The lesion involves the back of the torso and front of the torso · the photo was captured at an angle · the lesion is described as raised or bumpy and rough or flaky · reported lesion symptoms include itching, darkening and enlargement · the patient notes the condition has been present for more than one year:
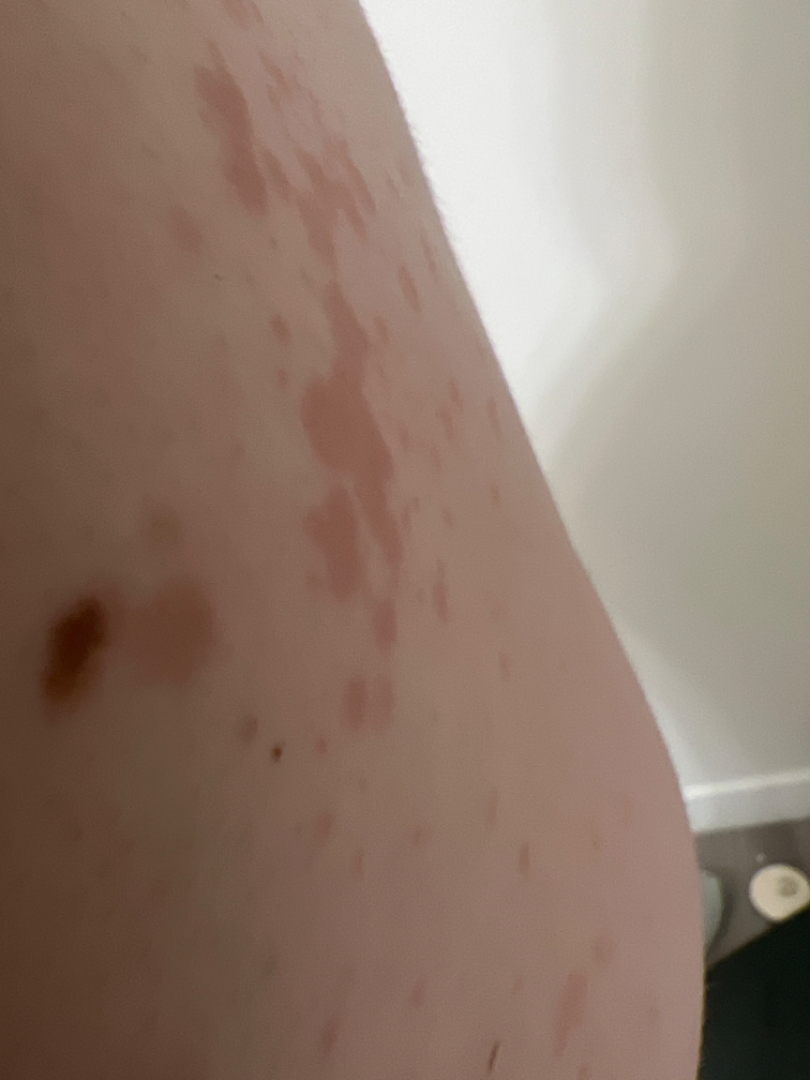On independent review by the dermatologists, the leading impression is Tinea Versicolor; a more distant consideration is Drug Rash; less likely is Seborrheic Dermatitis; less probable is Psoriasis.